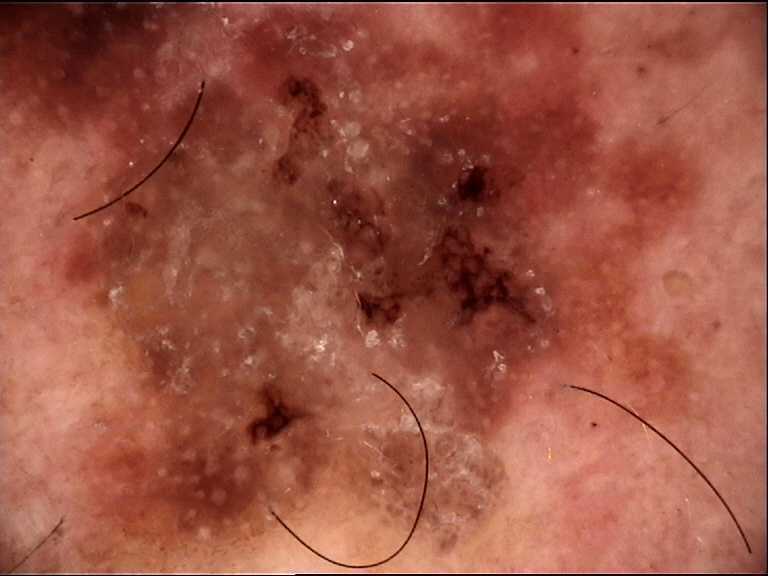Case:
• image · dermoscopy
• label · lentigo maligna (biopsy-proven)